Located on the arm; the condition has been present for less than one week; this image was taken at a distance; the patient notes the lesion is rough or flaky and raised or bumpy; the patient described the issue as a rash; female patient, age 30–39 — 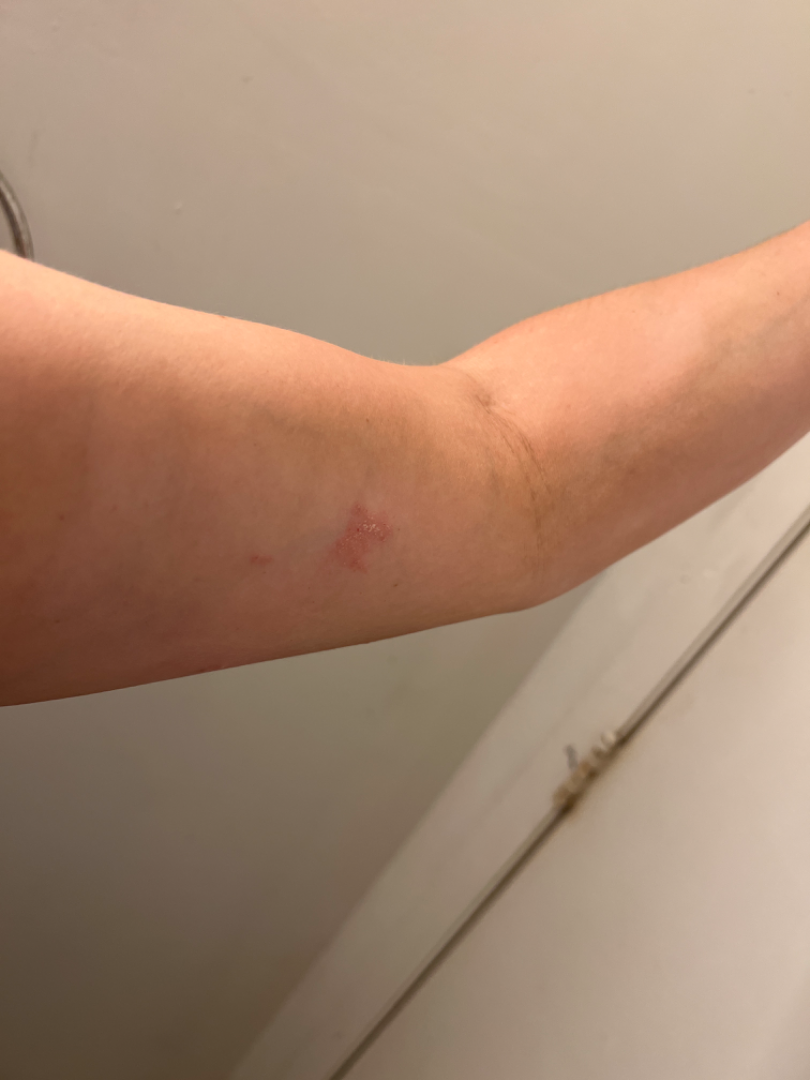The favored diagnosis is Allergic Contact Dermatitis; possibly Psoriasis; a more distant consideration is Eczema.